A female patient age 77 — 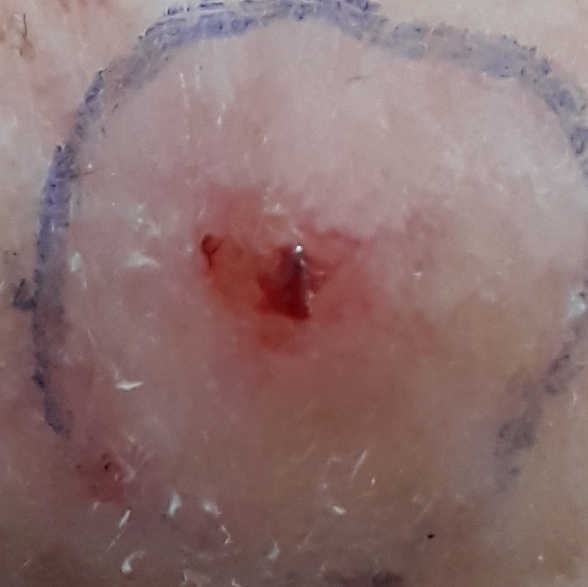Located on the nose.
The patient describes that the lesion is elevated, has bled, itches, and has grown.
The biopsy diagnosis was a basal cell carcinoma.